A skin lesion imaged with a dermatoscope; a female patient, approximately 80 years of age:
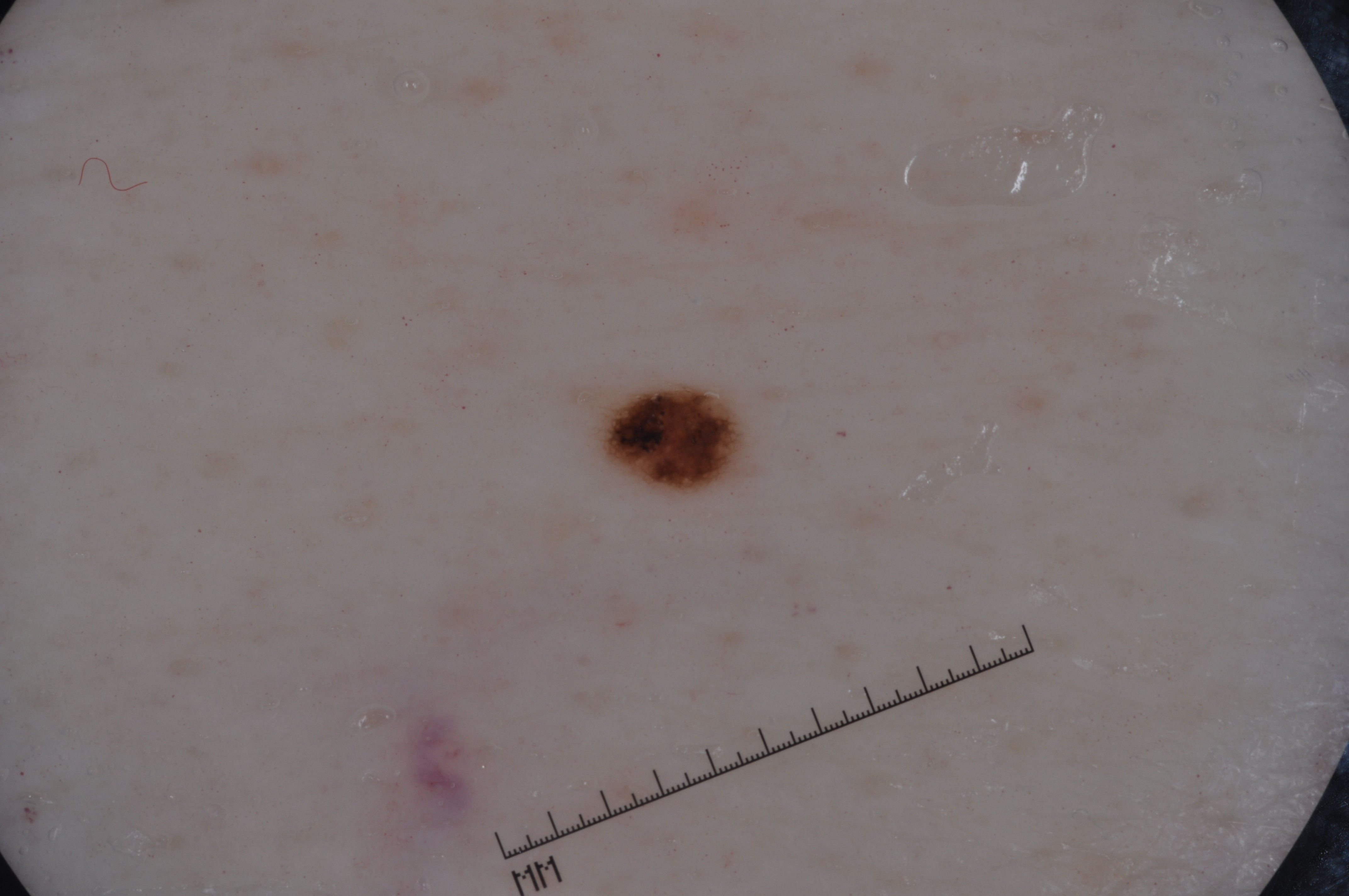Dermoscopic assessment notes pigment network and milia-like cysts; no negative network or streaks. The lesion occupies the region x1=601 y1=385 x2=738 y2=490. The clinical diagnosis was a melanocytic nevus, a benign lesion.